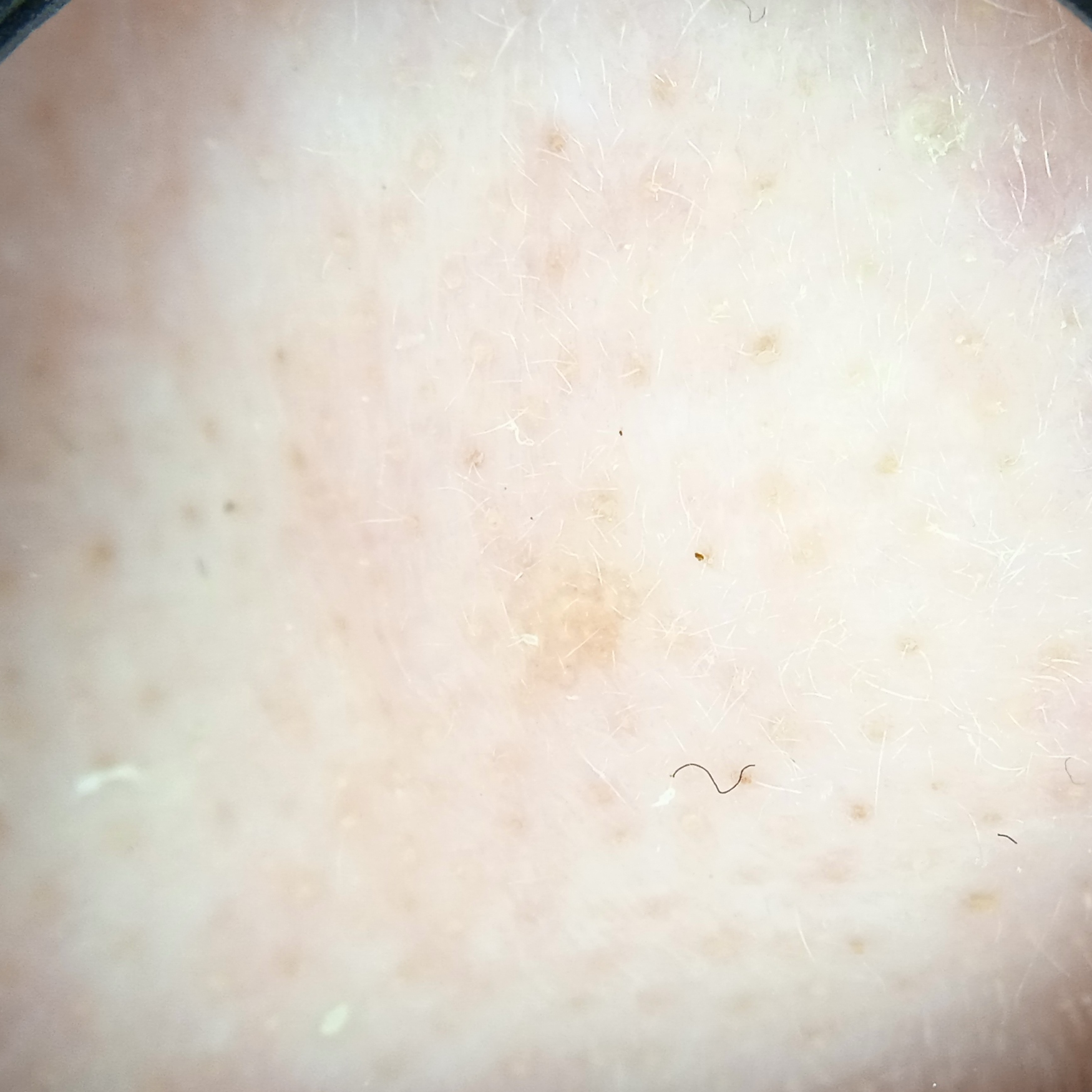The dermatologists' assessment was an actinic keratosis.